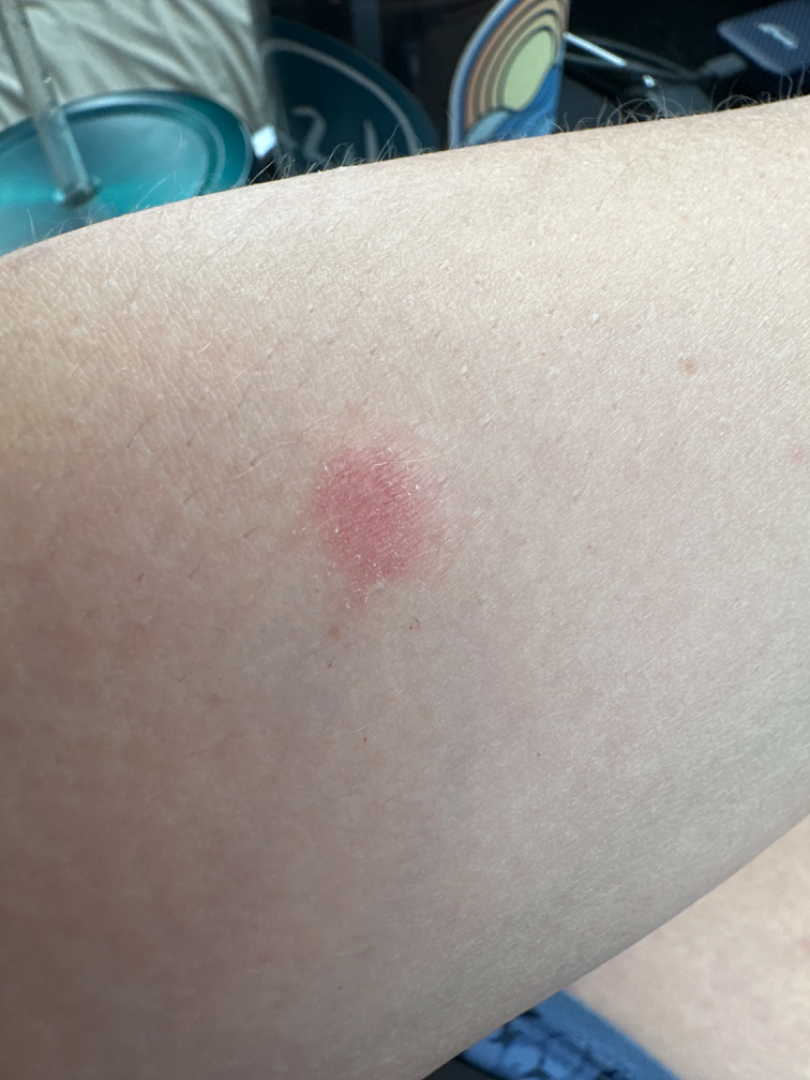Case summary:
• skin tone: Fitzpatrick phototype II; lay graders estimated Monk skin tone scale 1 or 2 (two reviewer pools)
• location: head or neck and arm
• shot type: close-up
• contributor: female, age 30–39
• patient-reported symptoms: itching
• present for: one to three months
• patient describes the issue as: a rash
• described texture: rough or flaky
• systemic symptoms: none reported
• assessment: the leading impression is Eczema